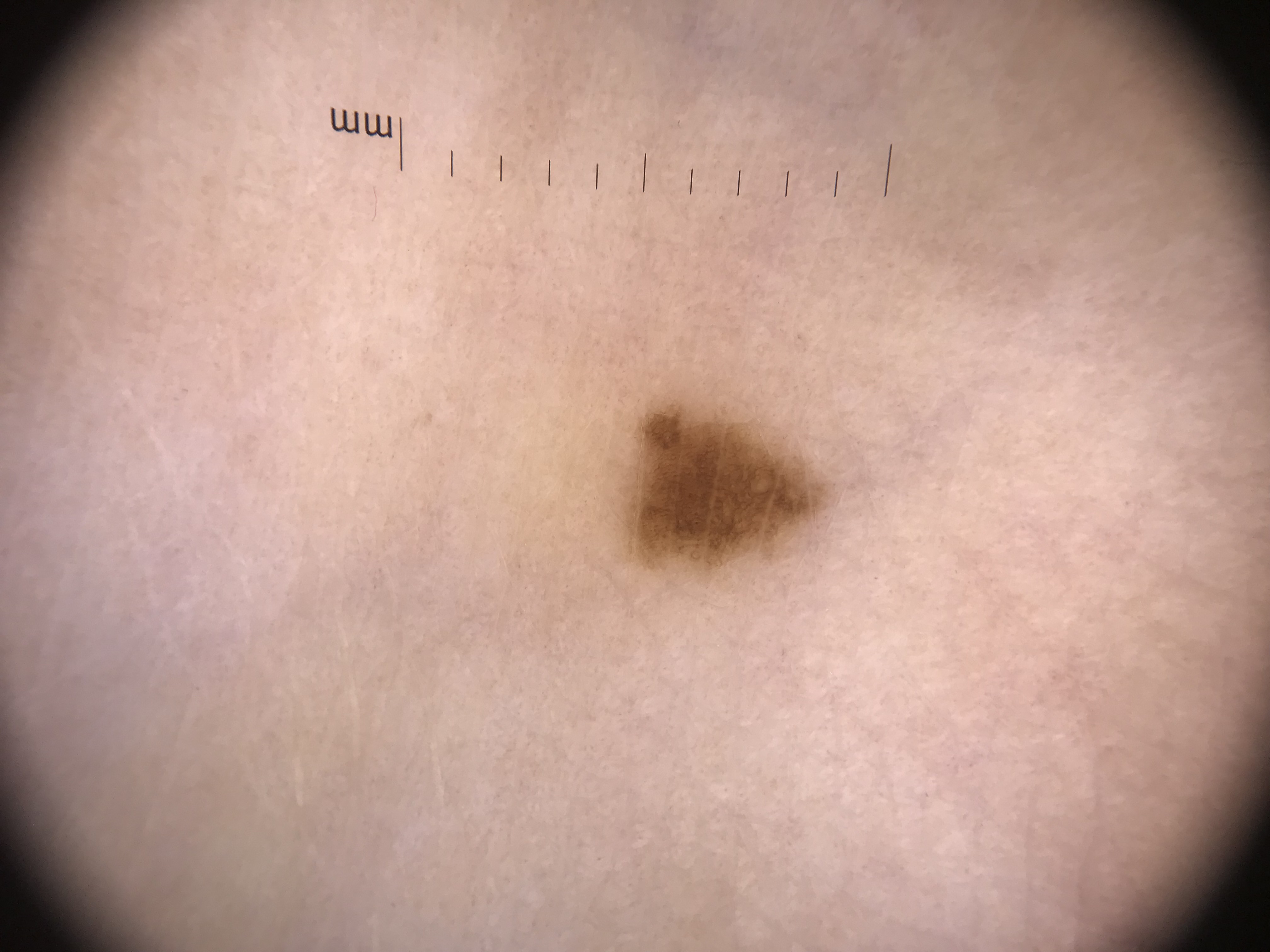Summary: A dermoscopic close-up of a skin lesion. Impression: Classified as a dysplastic junctional nevus.